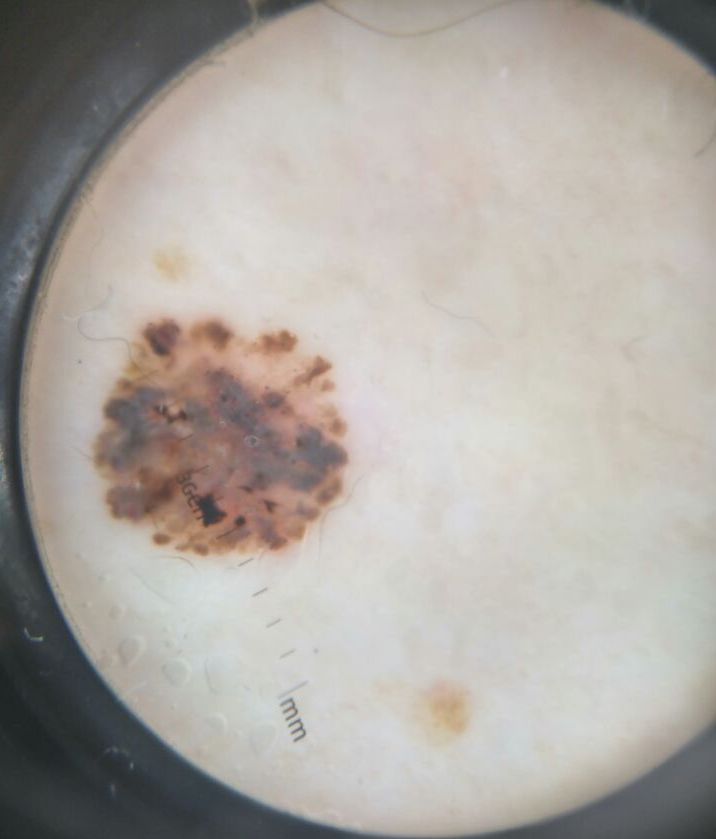A dermoscopic image of a skin lesion.
Histopathology confirmed a keratinocytic lesion — a basal cell carcinoma.